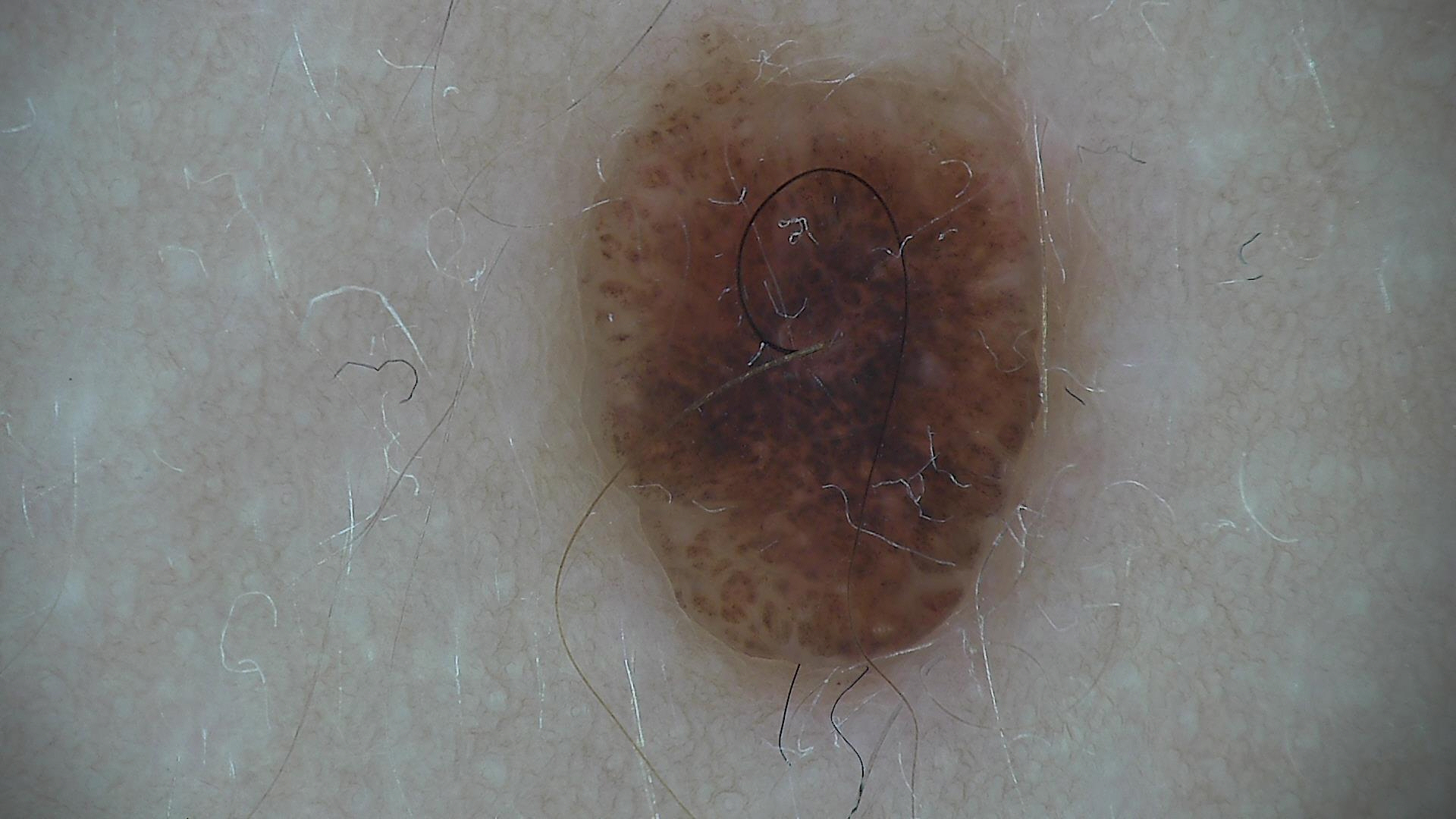Classified as a dermal nevus.